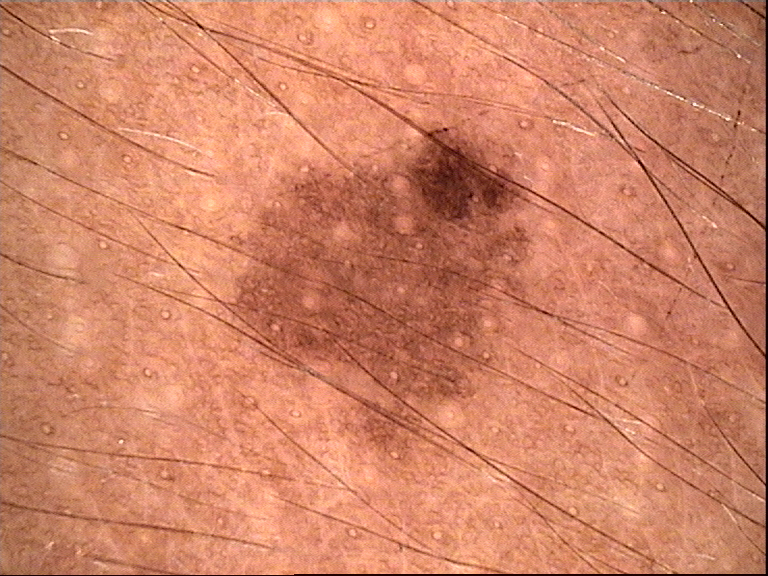Labeled as a dysplastic junctional nevus.